A dermoscopic close-up of a skin lesion · a female patient, aged approximately 35 — 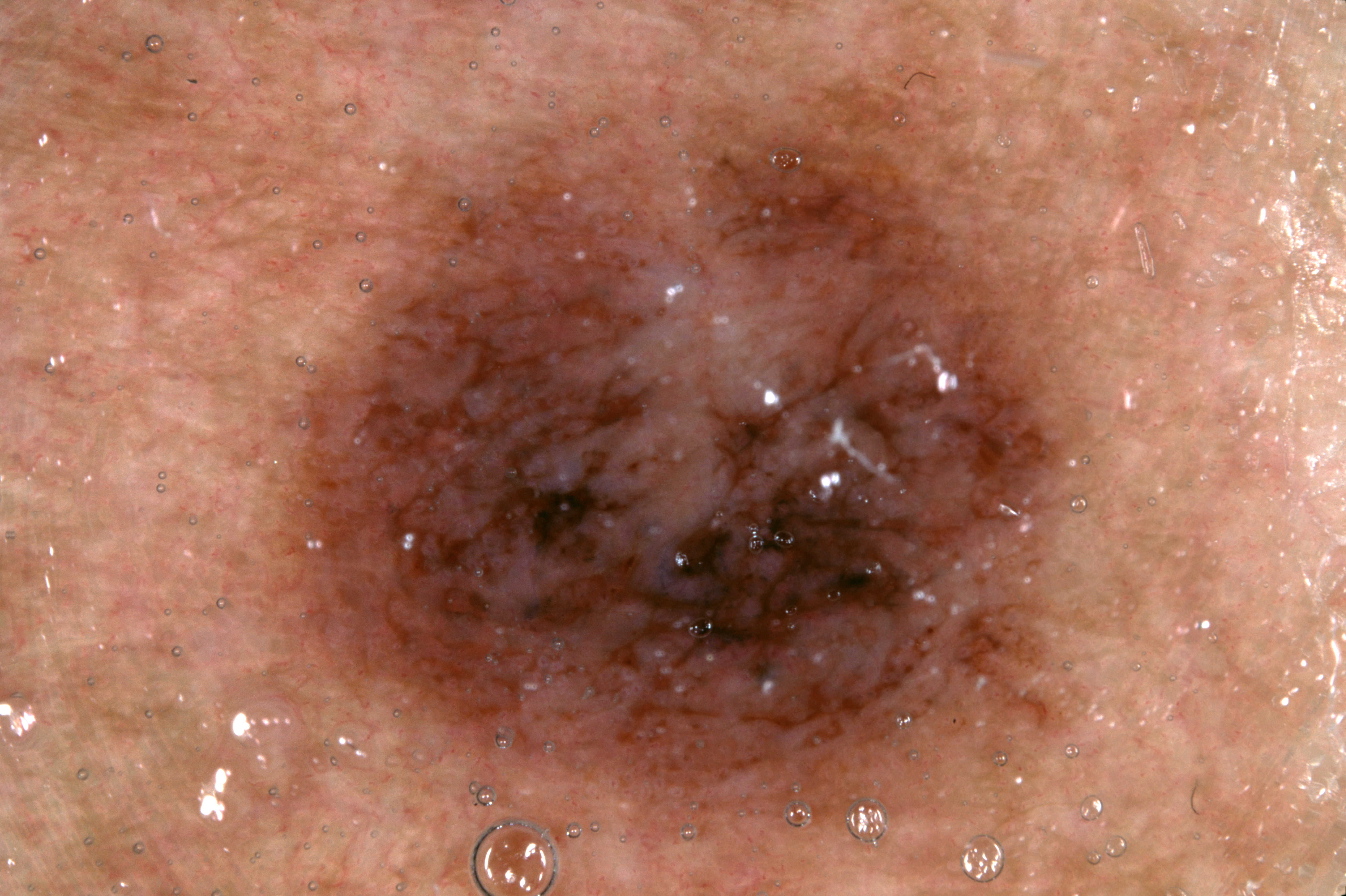| field | value |
|---|---|
| bounding box | 263, 70, 1093, 854 |
| lesion extent | ~43% of the field |
| absent dermoscopic findings | milia-like cysts, negative network, streaks, and pigment network |
| diagnostic label | a melanocytic nevus |